The affected area is the arm and leg; the contributor is a male aged 40–49; this is a close-up image.
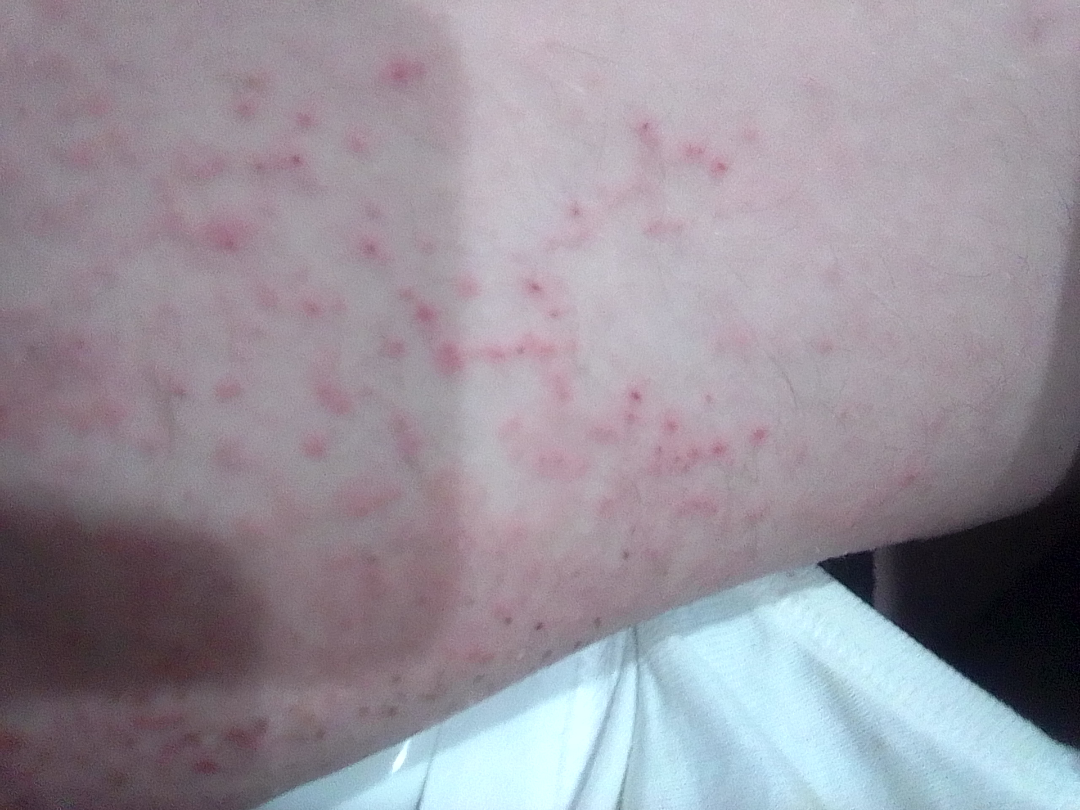Skin tone: Fitzpatrick II; non-clinician graders estimated a Monk Skin Tone of 1.
The patient described the issue as a rash.
The patient reports itching.
The patient reports the lesion is rough or flaky.
Most consistent with Eczema.